The patient is a female aged 40–49, close-up view:
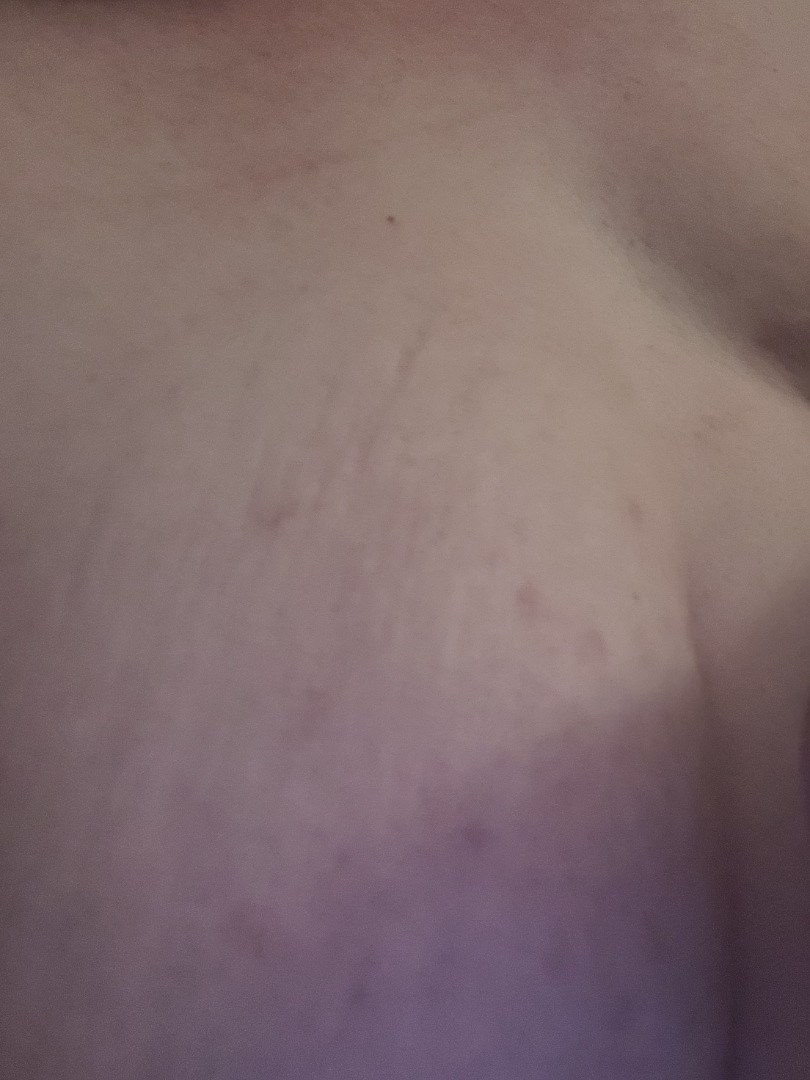The case was difficult to assess from the available photograph.